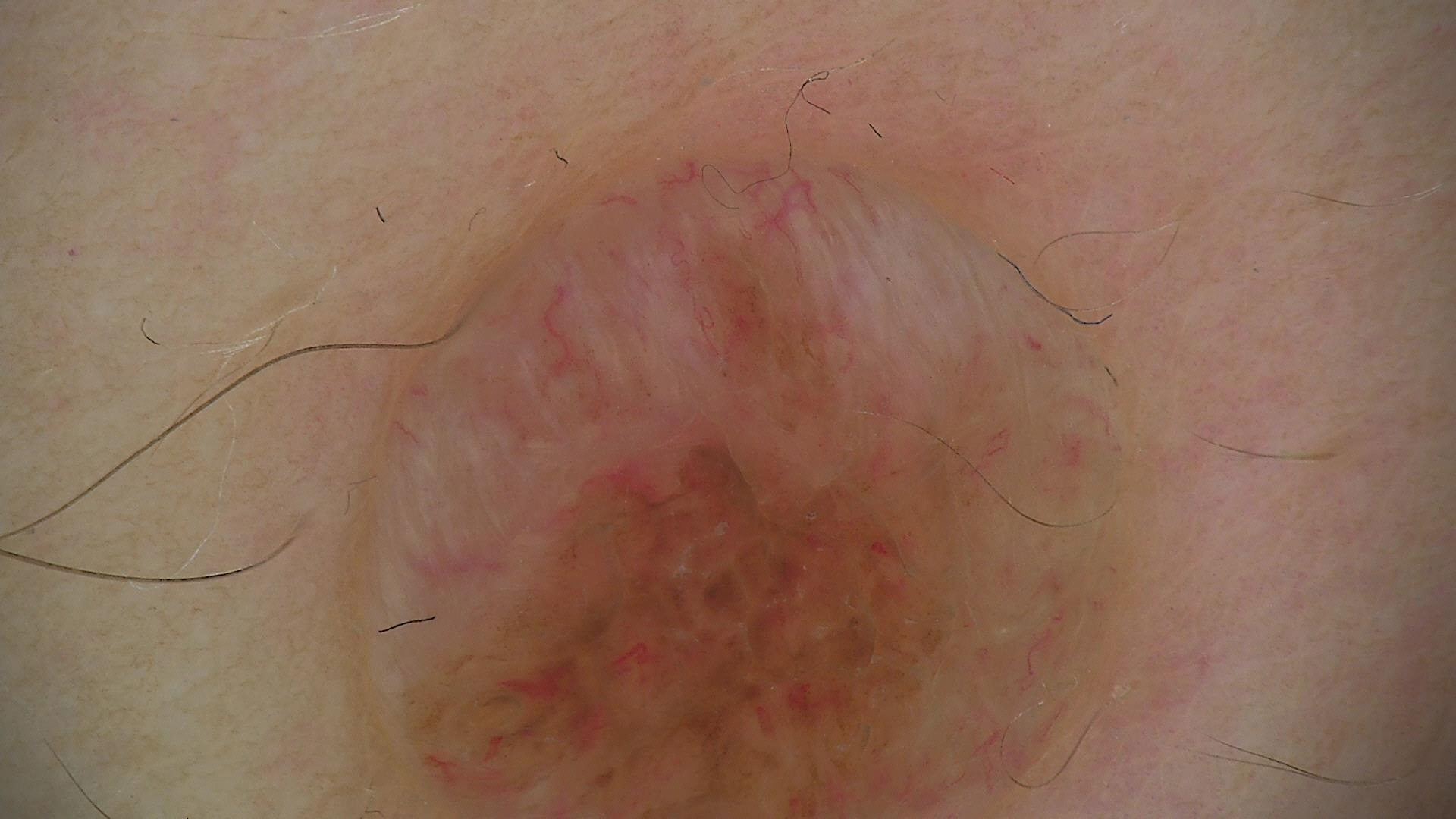This is a banal lesion. Labeled as a dermal nevus.